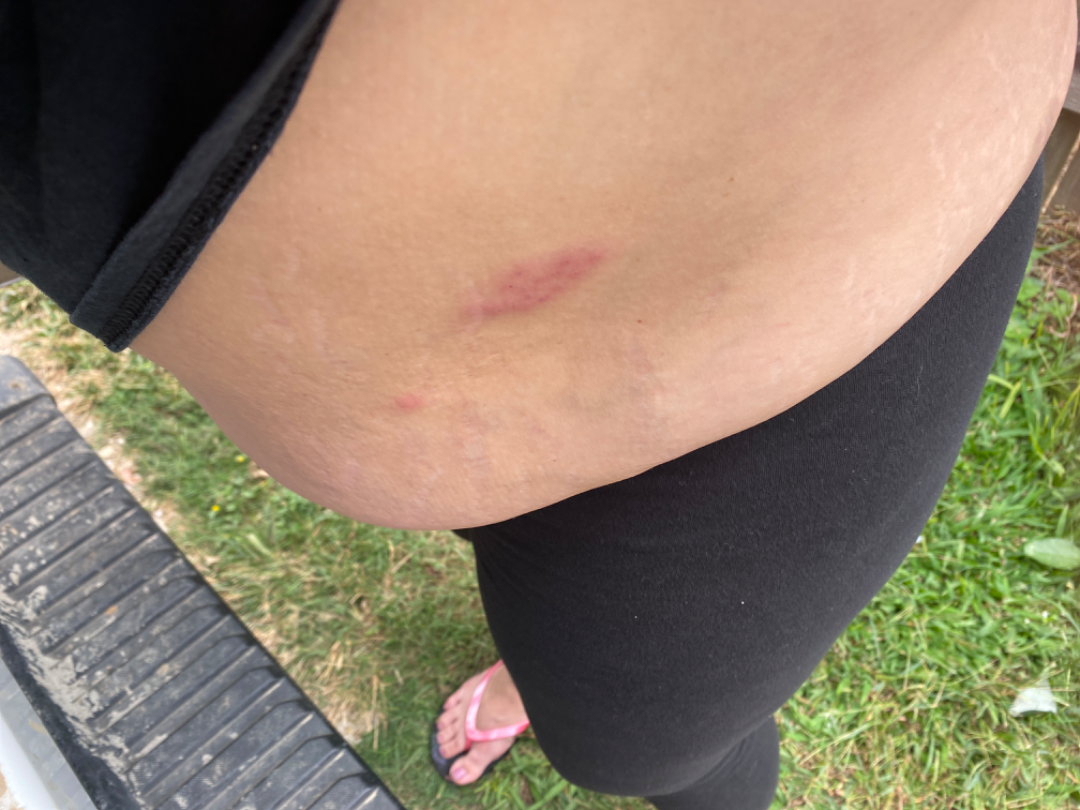<summary>
<shot_type>at a distance</shot_type>
<body_site>front of the torso</body_site>
<differential>
  <leading>Herpes Zoster</leading>
  <considered>Herpes Simplex</considered>
  <unlikely>Allergic Contact Dermatitis</unlikely>
</differential>
</summary>